A dermoscopic image of a skin lesion; a female subject, aged approximately 70.
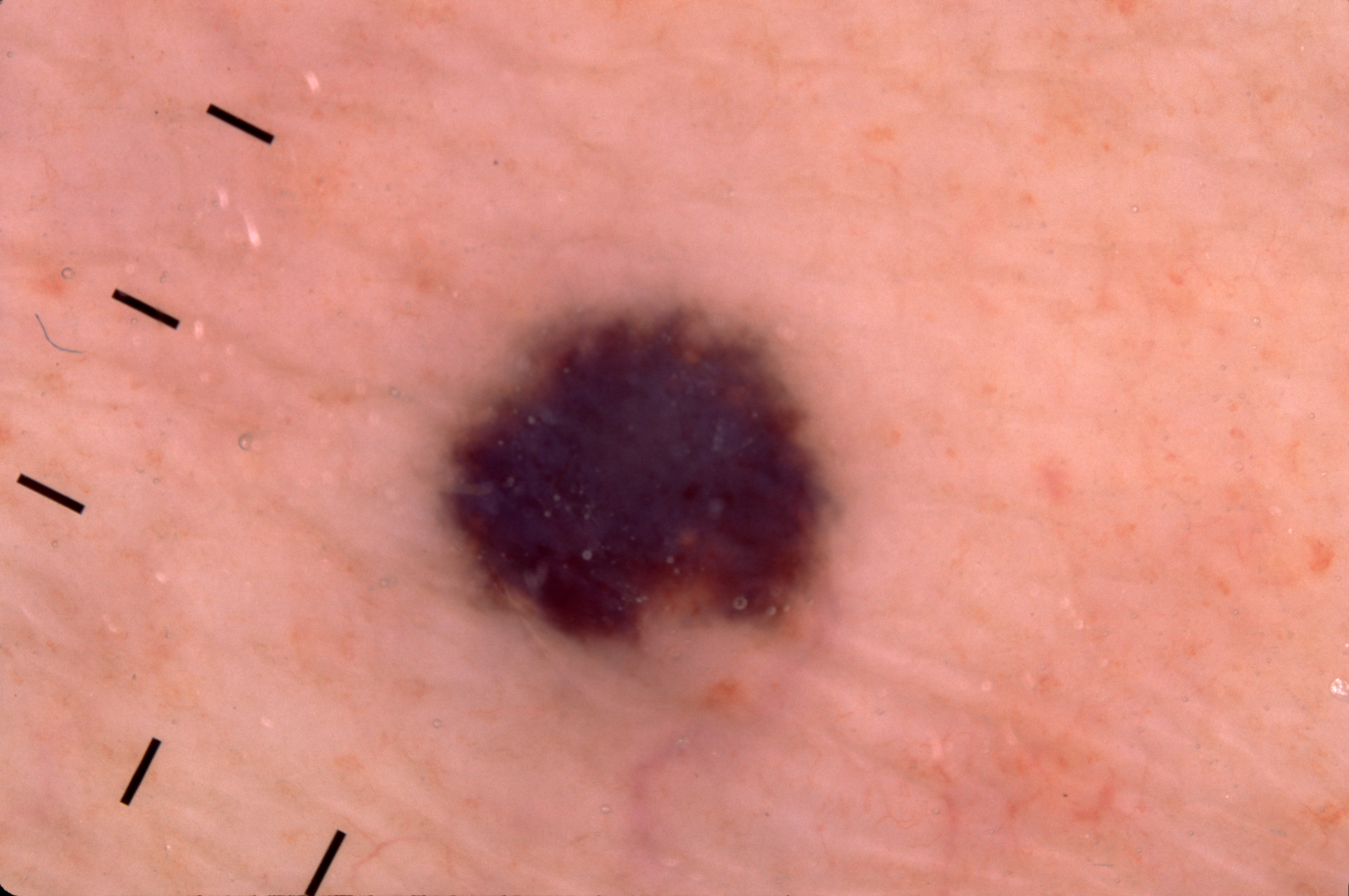Dermoscopic assessment notes no streaks, pigment network, milia-like cysts, or negative network.
The lesion covers approximately 10% of the dermoscopic field.
In (x1, y1, x2, y2) order, the lesion spans <bbox>415, 293, 846, 721</bbox>.
Consistent with a melanocytic nevus.